A female subject approximately 15 years of age; this is a dermoscopic photograph of a skin lesion: 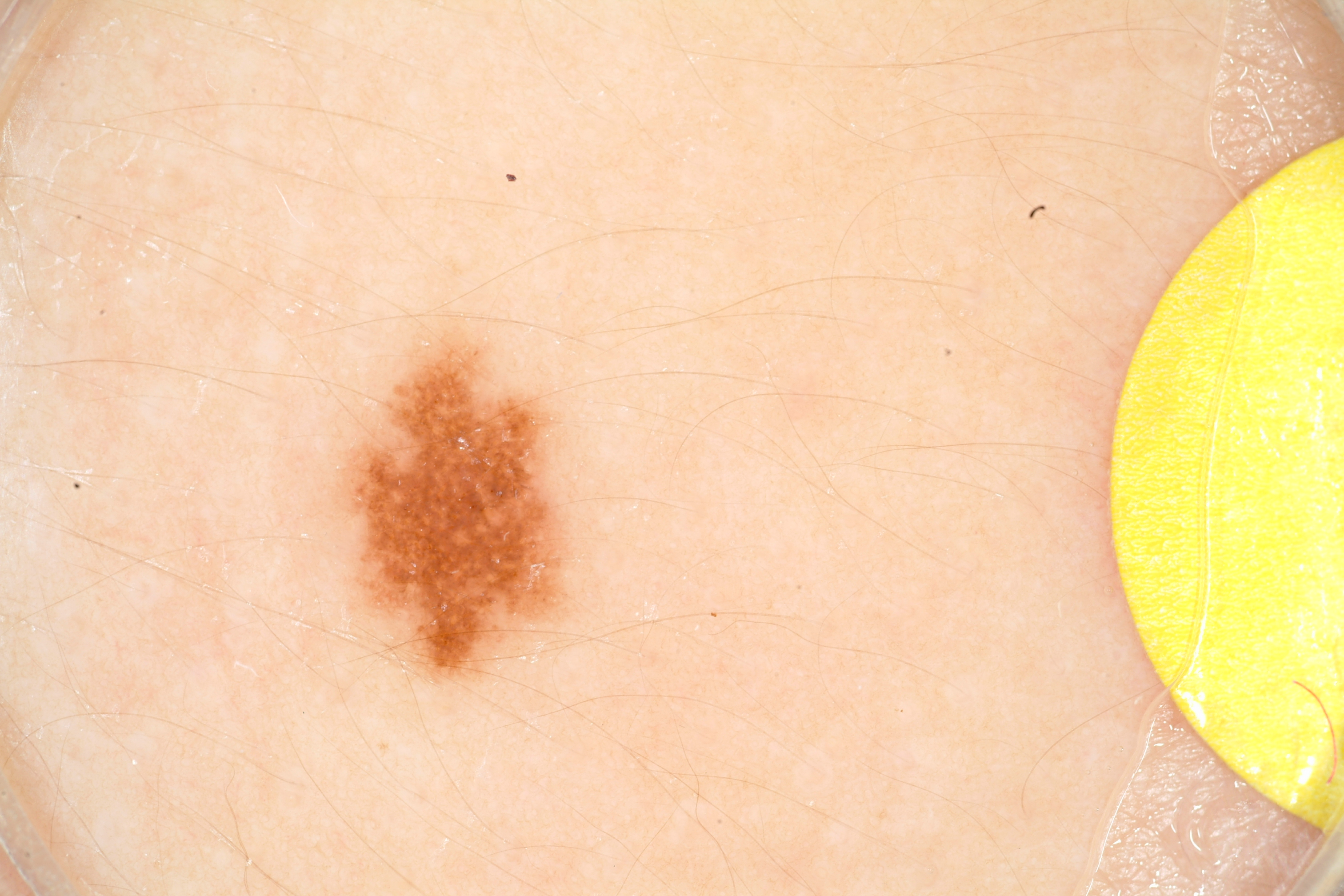The lesion takes up about 6% of the image. Dermoscopic examination shows no negative network, globules, milia-like cysts, pigment network, or streaks. As (left, top, right, bottom), lesion location: <box>306, 314, 598, 701</box>. The clinical diagnosis was a melanocytic nevus.